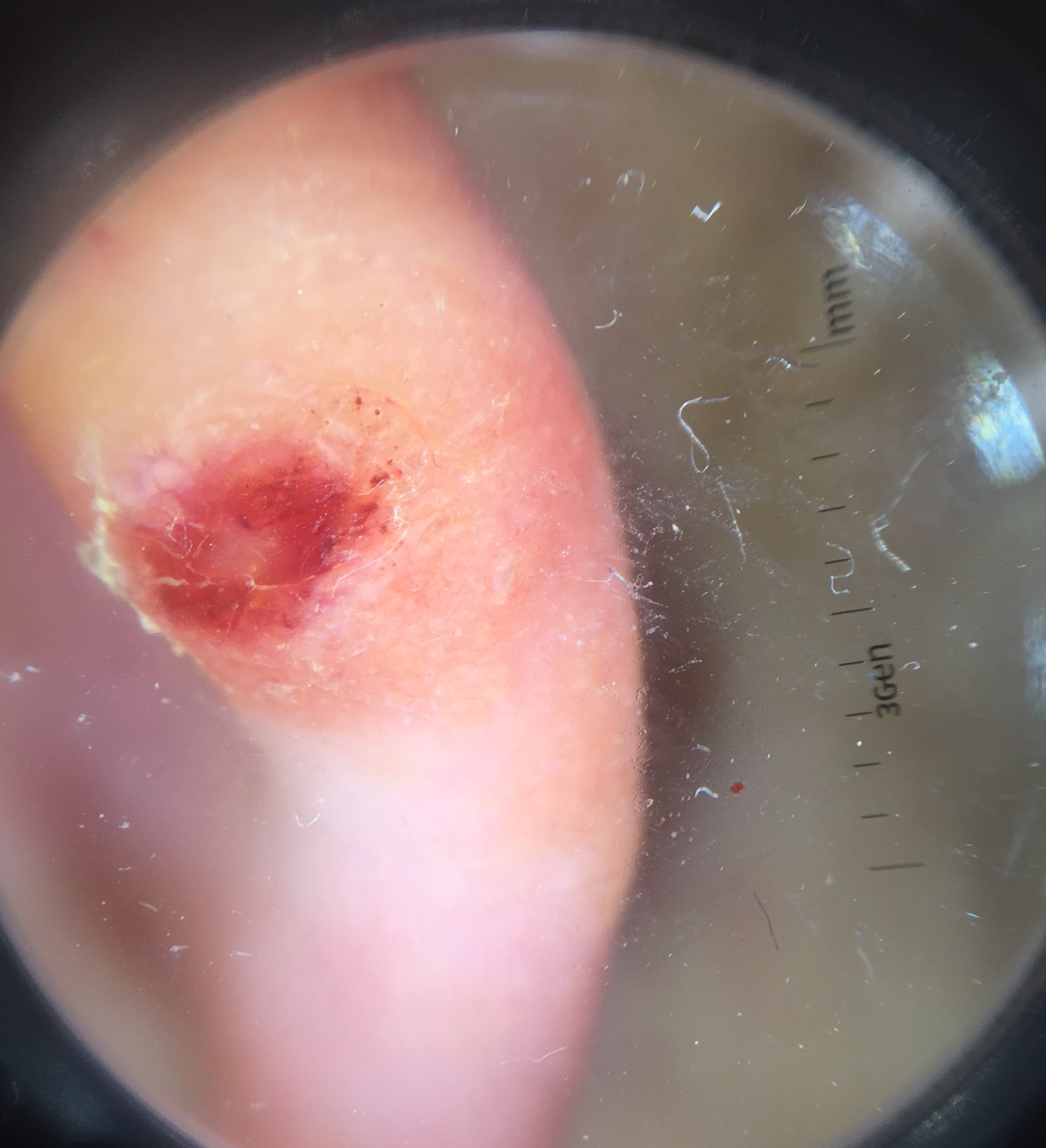Diagnosis: Biopsy-confirmed as a squamous cell carcinoma.